Located on the front of the torso, head or neck, back of the hand, palm, sole of the foot, top or side of the foot, leg and arm. The photograph was taken at a distance:
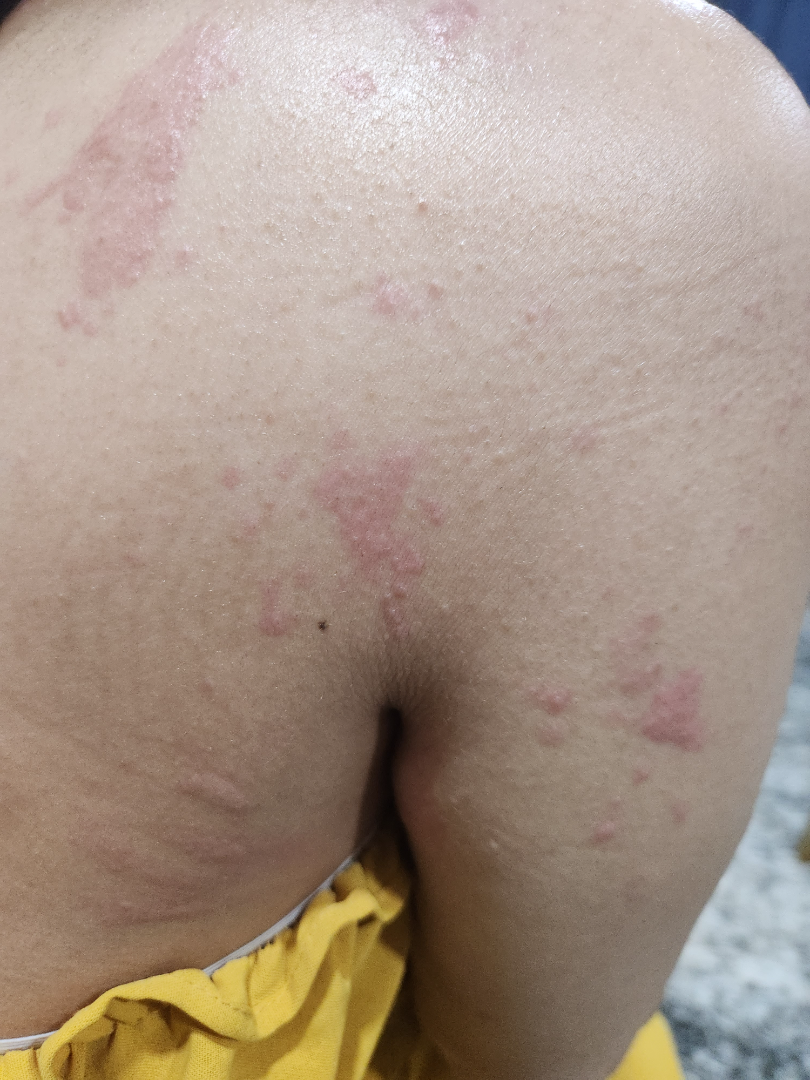Symptoms reported: burning and itching. Reported duration is less than one week. Texture is reported as raised or bumpy. On remote review of the image, the leading impression is Allergic Contact Dermatitis; also consider Herpes Zoster.